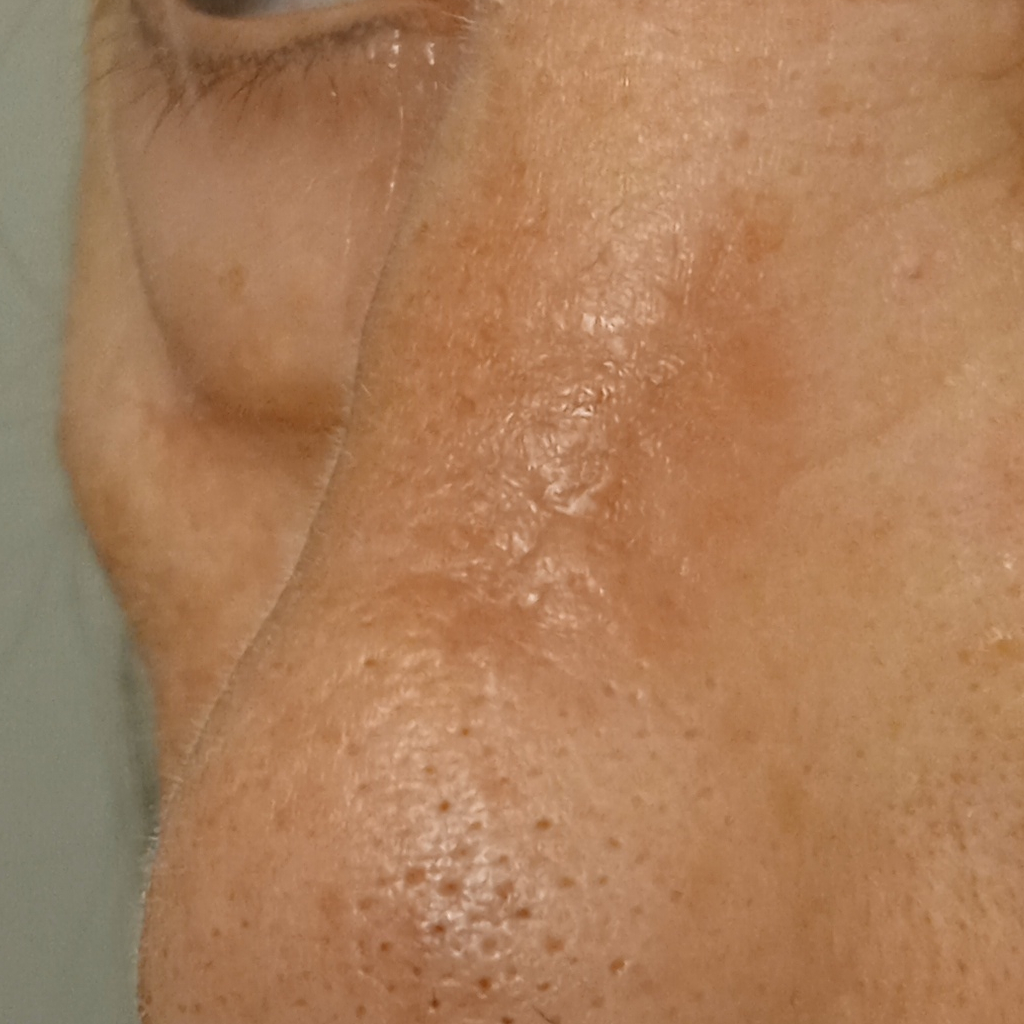Findings: A macroscopic clinical photograph of a skin lesion. The patient says their skin tans without first burning. A female subject age 68. Imaged for a research study, with no referral diagnosis recorded. Few moles overall by the patient's own estimate. The lesion involves the face. Impression: The dermatologists' assessment was an actinic keratosis.